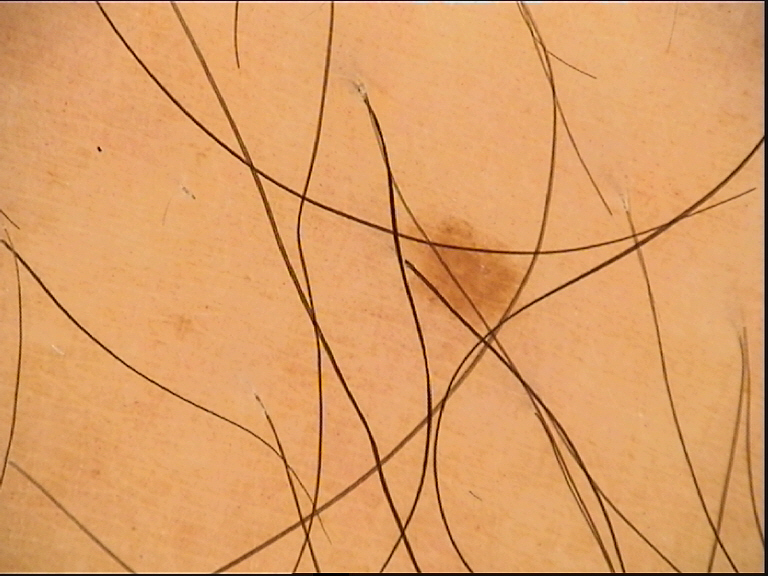class — junctional nevus (expert consensus).